Dermoscopy of a skin lesion:
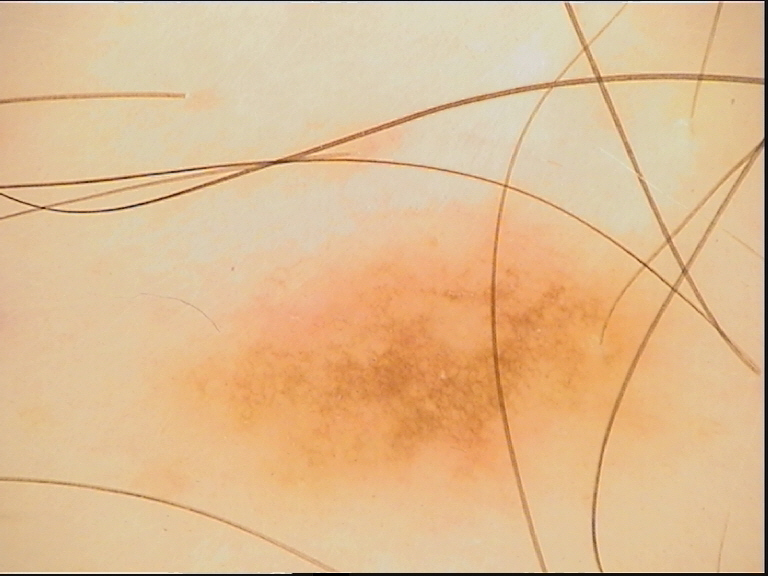Conclusion: The diagnostic label was a dysplastic junctional nevus.